A dermoscopic image of a skin lesion.
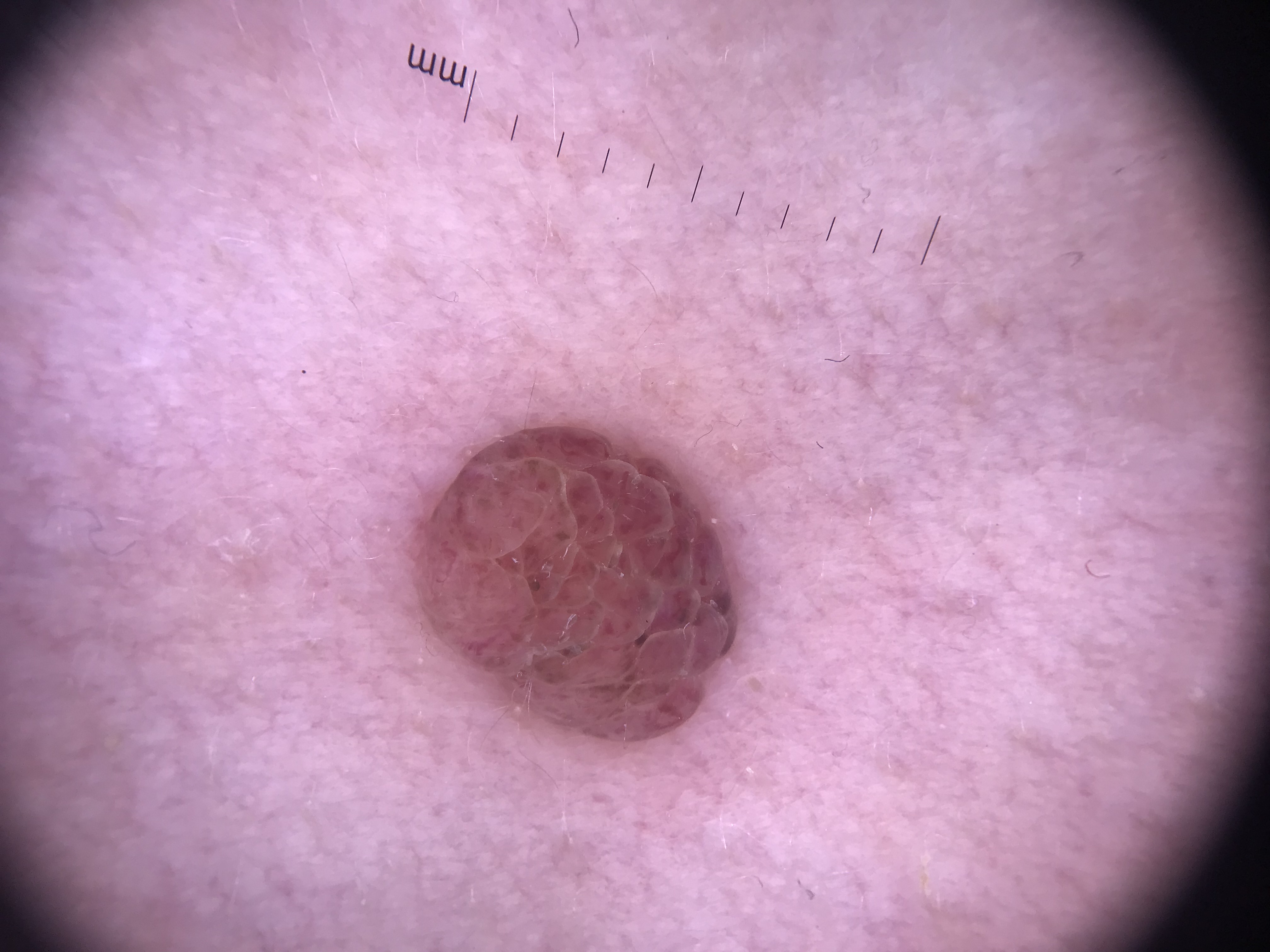classification = banal; diagnosis = dermal nevus (expert consensus).